A dermoscopic image of a skin lesion: 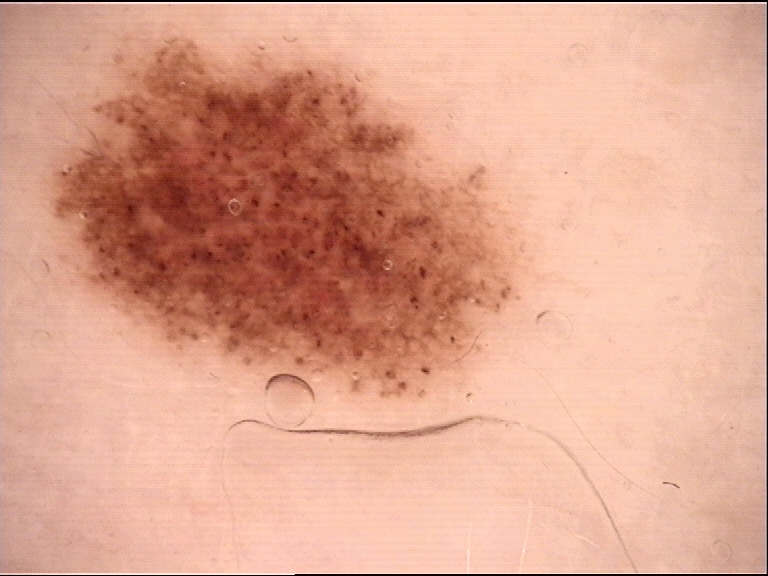Consistent with a dysplastic compound nevus.